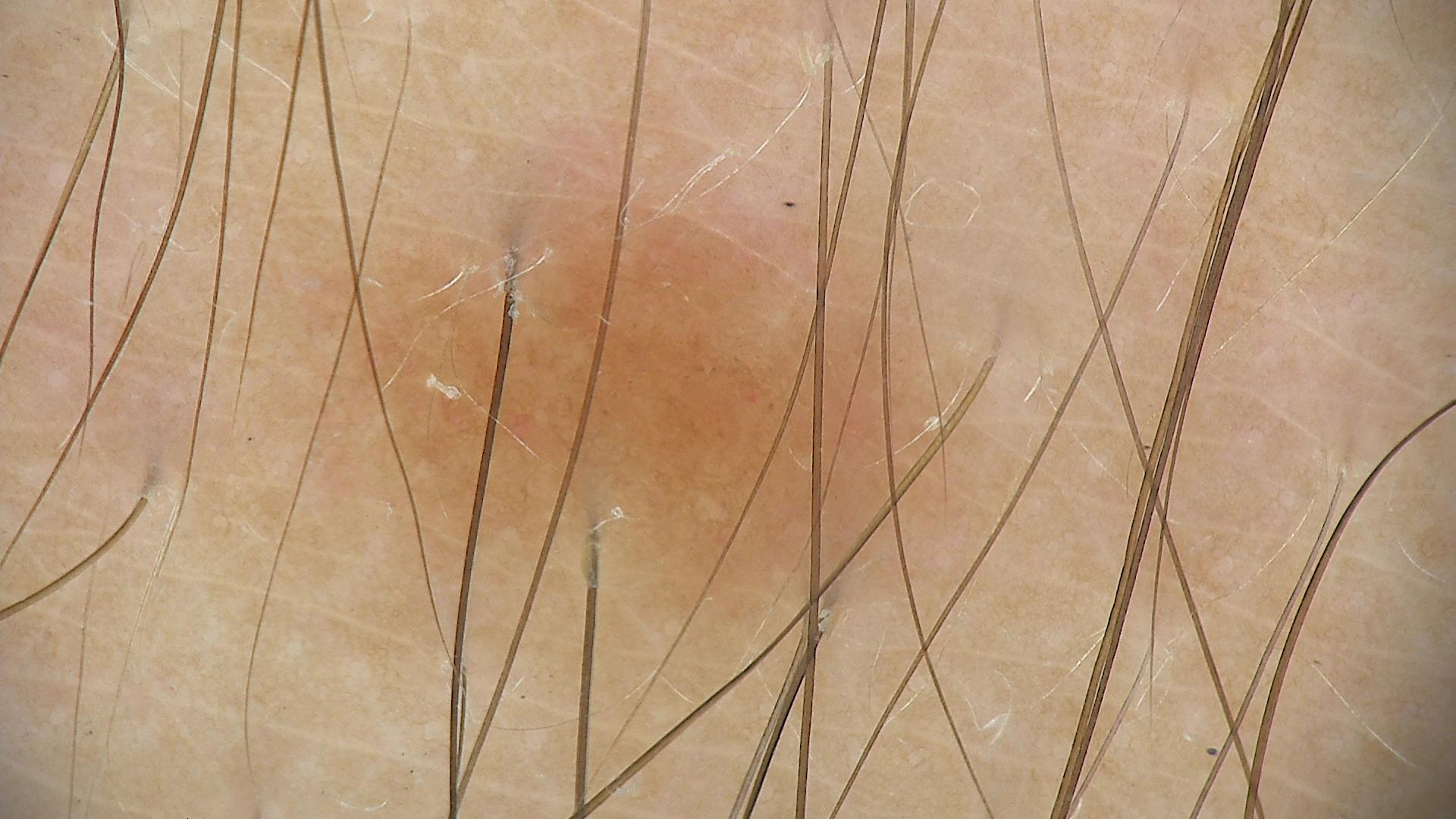assessment: dysplastic junctional nevus (expert consensus).